This image was taken at a distance. The contributor is 18–29, female — 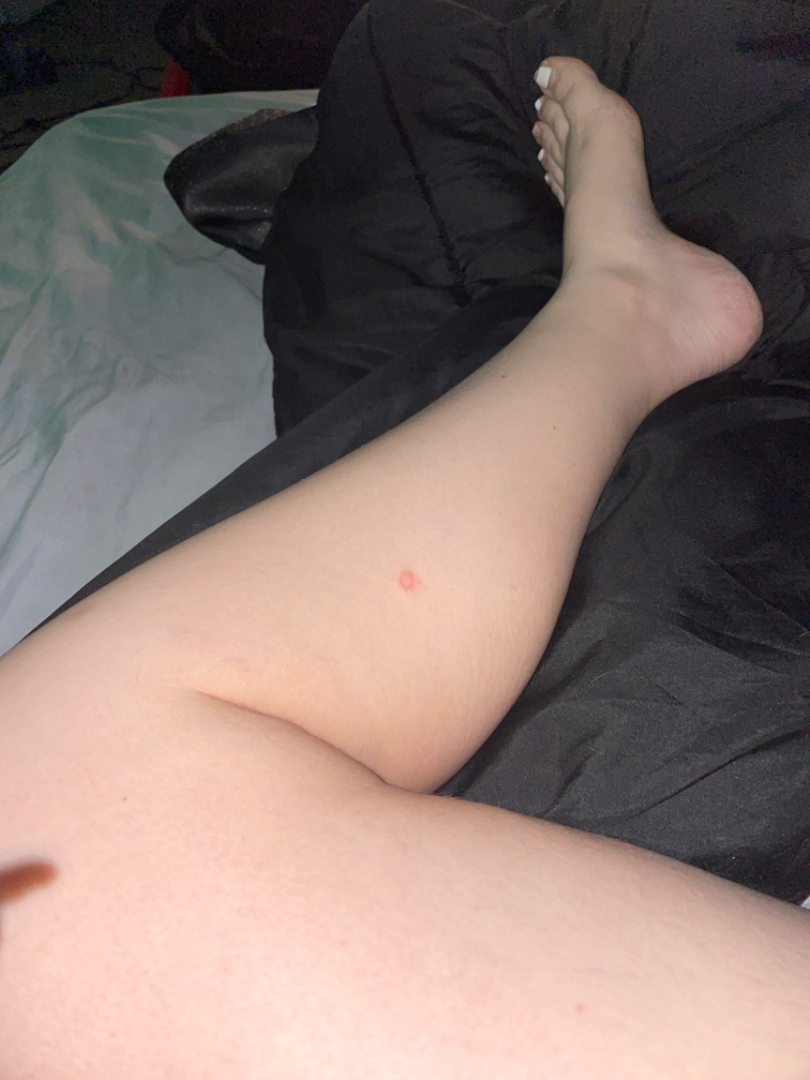Findings: The case was indeterminate on photographic review.